The arm and leg are involved · close-up view.
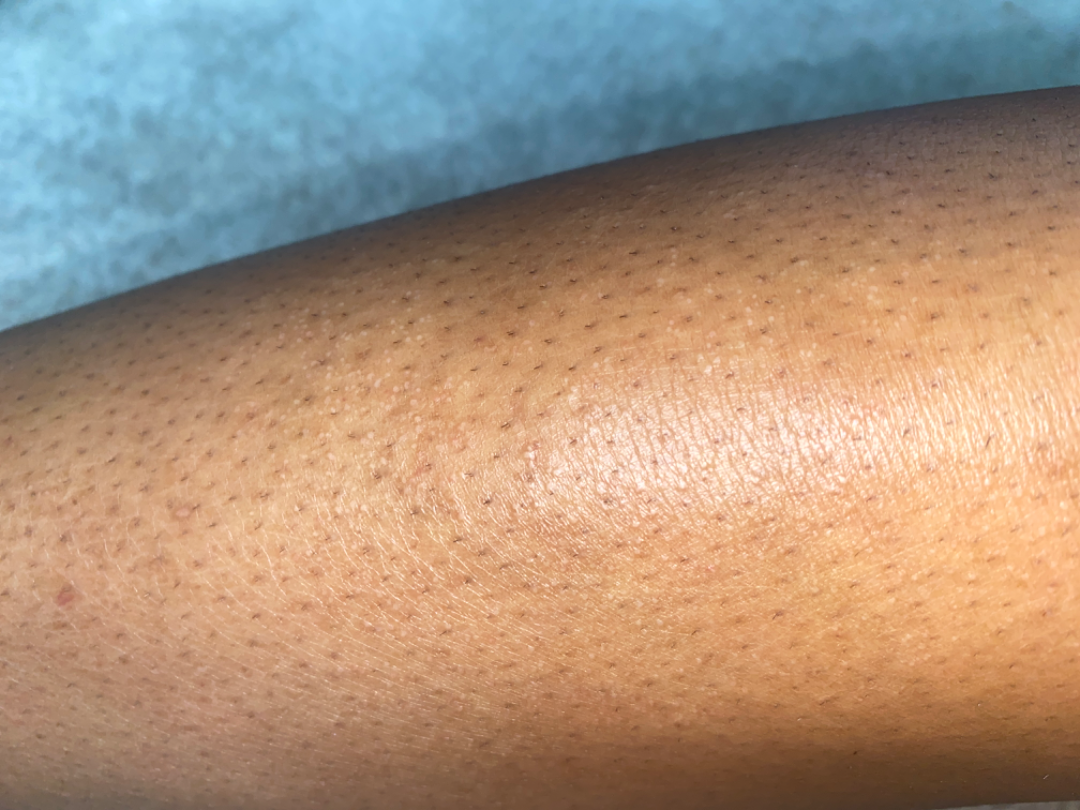The patient described the issue as a rash. Present for one to four weeks. Fitzpatrick phototype II; lay reviewers estimated MST 5–6. No relevant lesion symptoms reported. The differential is split between Eczema and Xerosis.